A dermoscopy image of a single skin lesion.
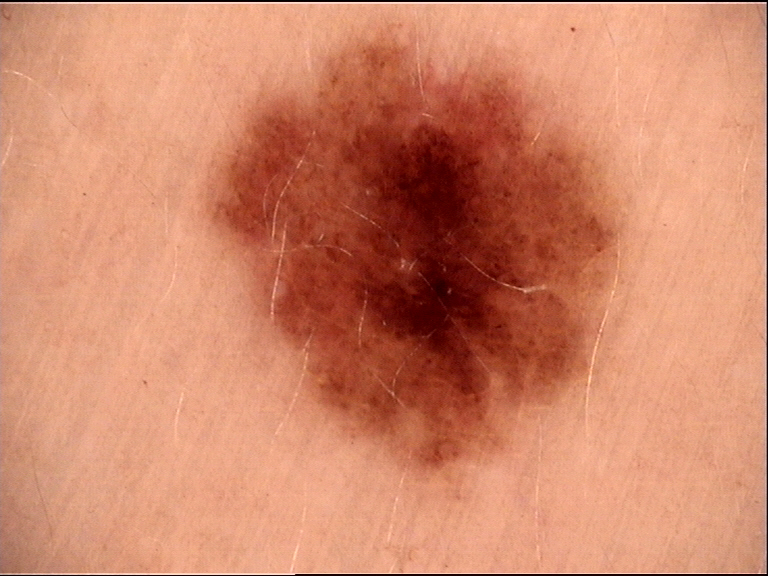Impression:
The diagnosis was a dysplastic junctional nevus.